This is a close-up image · the lesion involves the arm · the contributor is 50–59, female:
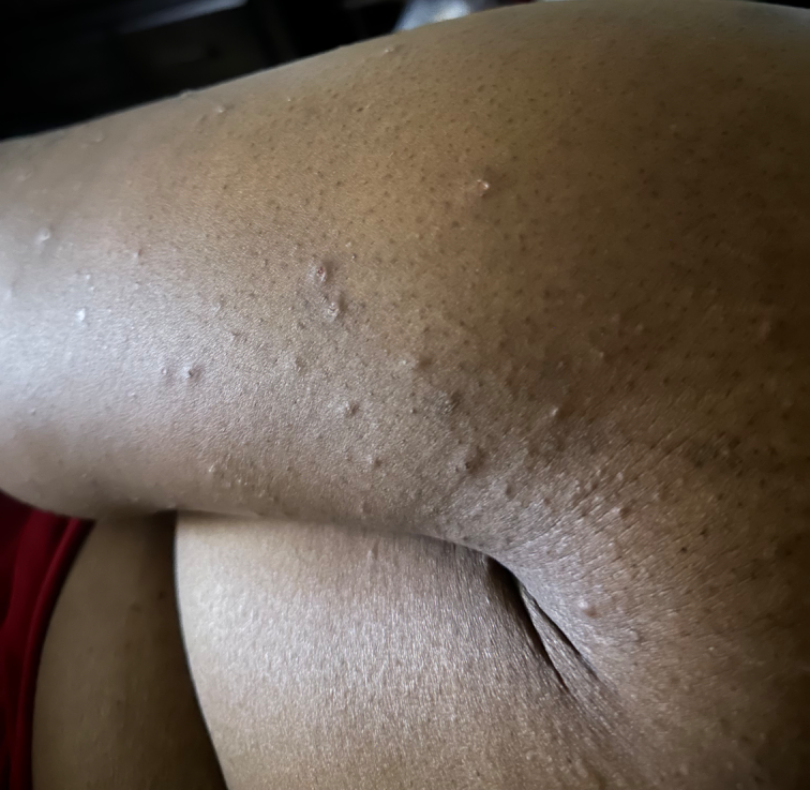differential:
  leading:
    - Prurigo nodularis
  considered:
    - Eczema